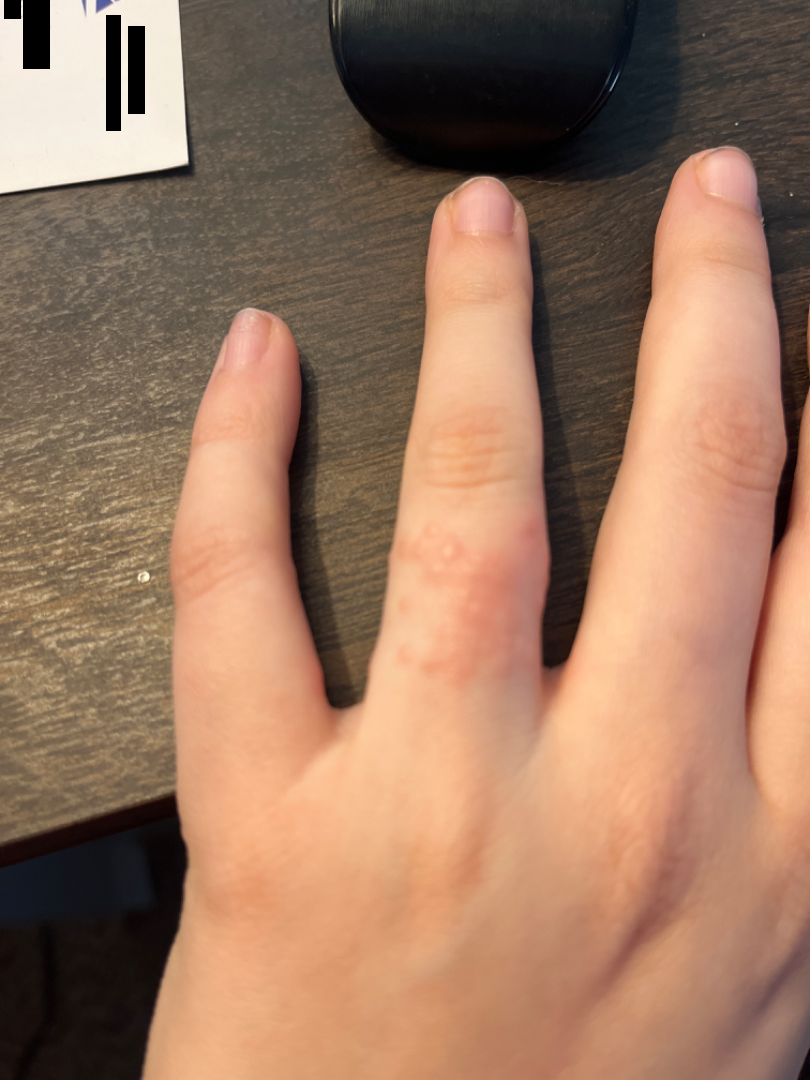Skin tone: FST II. Close-up view. The contributor is a female aged 18–29. Self-categorized by the patient as a rash. Located on the back of the hand. The condition has been present for less than one week. On remote dermatologist review, Allergic Contact Dermatitis (100%).